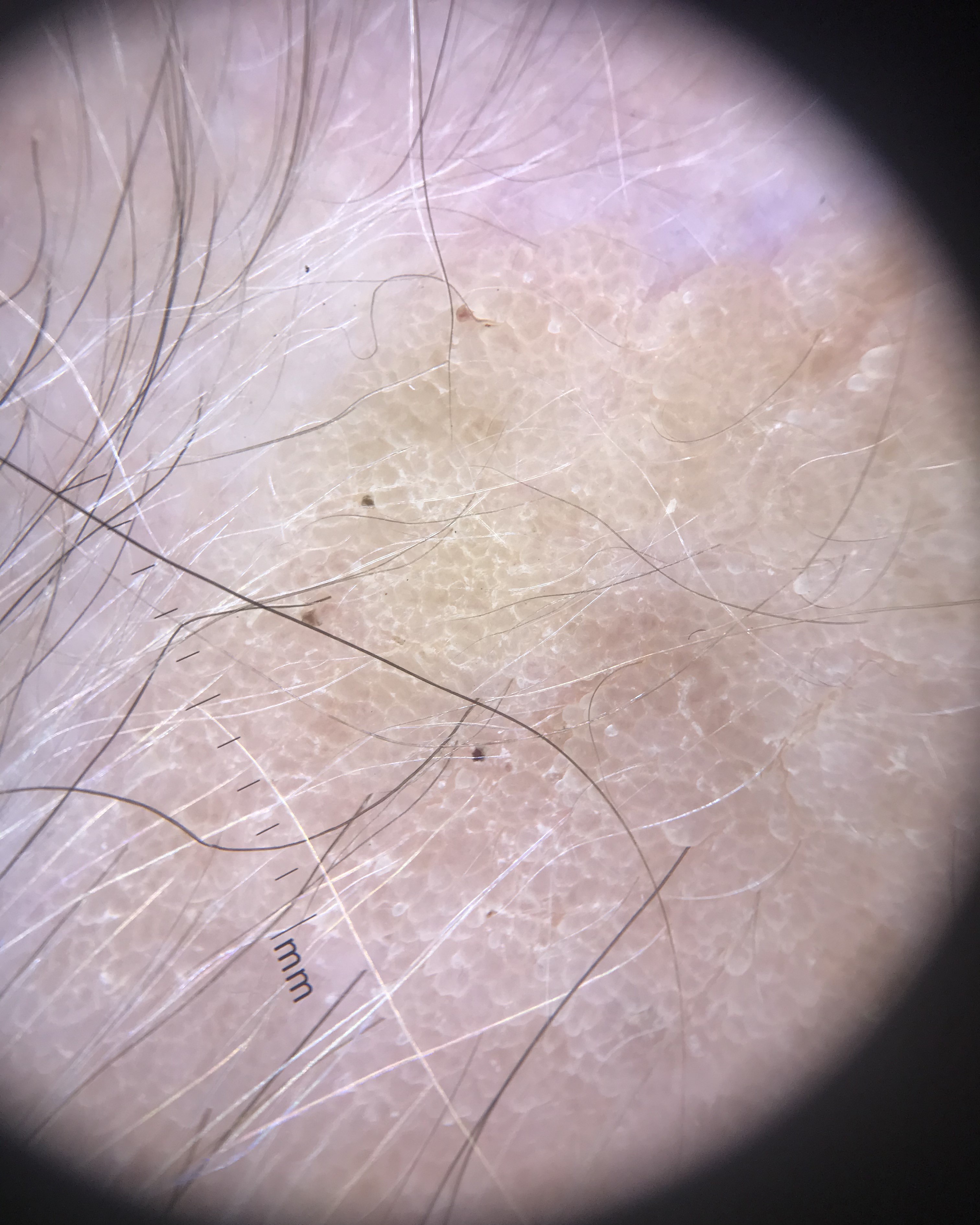Findings: A dermoscopic close-up of a skin lesion. Impression: Classified as a keratinocytic lesion — a seborrheic keratosis.